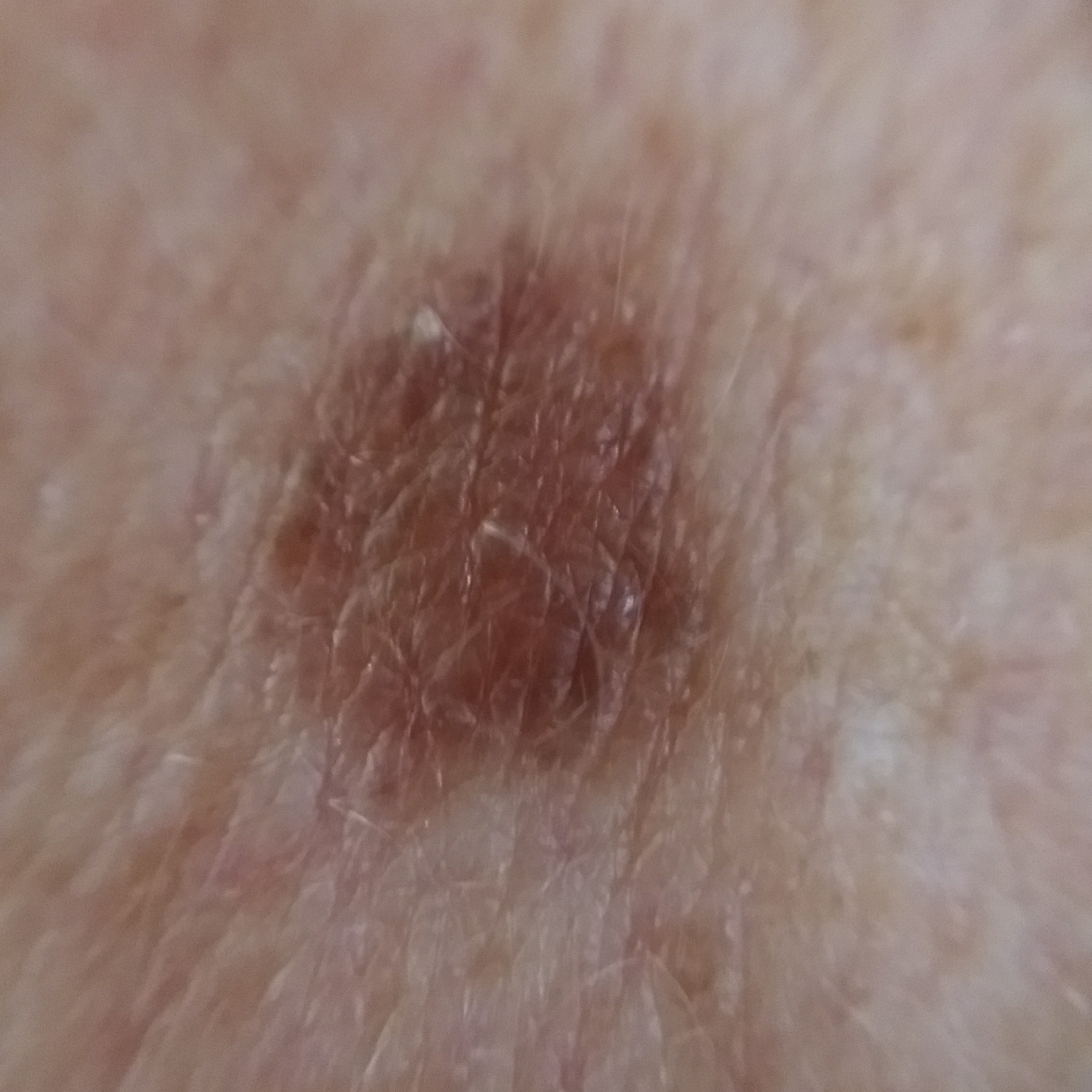The patient was assessed as skin type III. A male patient aged 61. Located on the back. The lesion is roughly 2 by 2 mm. The diagnostic impression was a nevus.